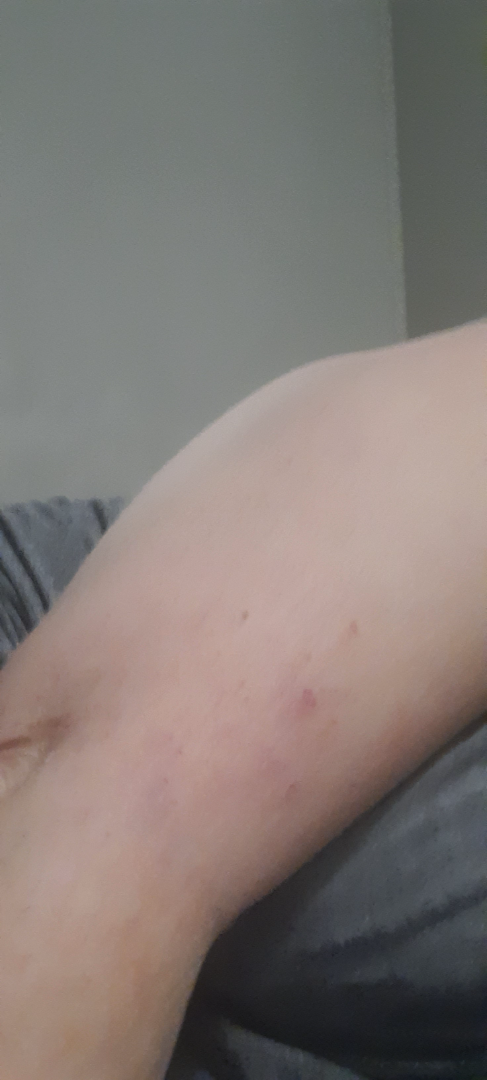{"assessment": "not assessable"}